The affected area is the front of the torso, back of the torso and arm; this is a close-up image; the patient is a male aged 30–39.
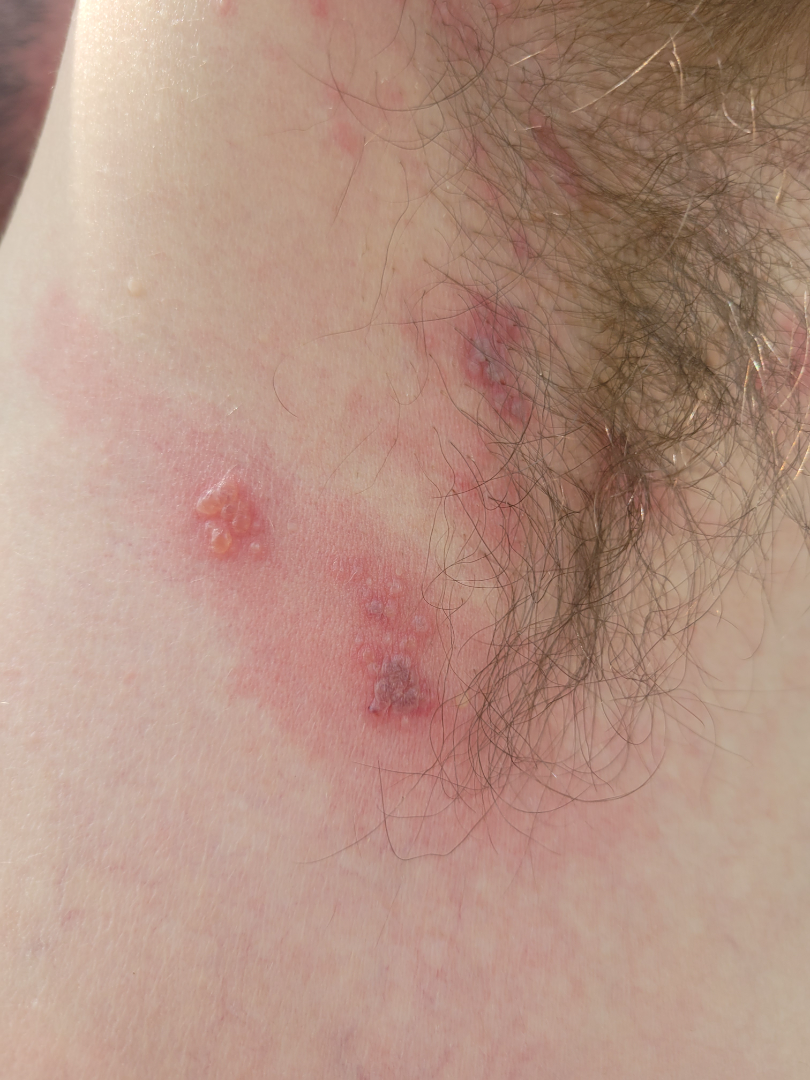{"differential": {"tied_lead": ["Herpes Zoster", "Herpes Simplex"]}}